This is a dermoscopic photograph of a skin lesion.
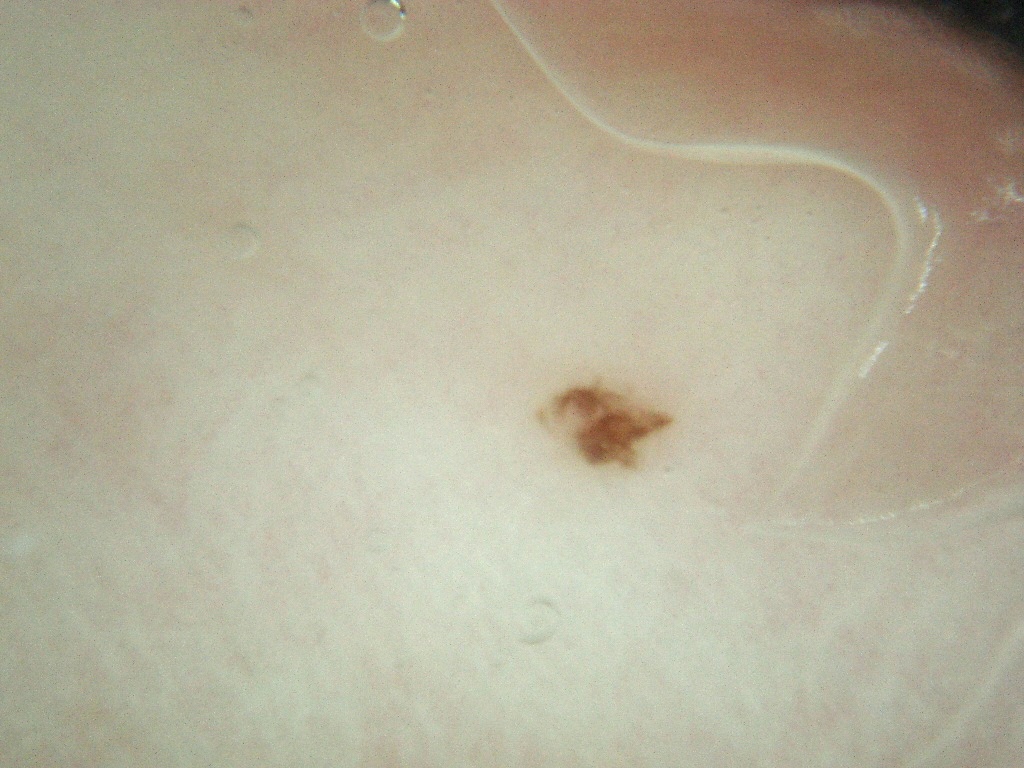Q: Where is the lesion in the image?
A: [535,373,674,470]
Q: Which dermoscopic features are absent?
A: globules and streaks
Q: How much of the field does the lesion occupy?
A: ~1% of the field
Q: What is this lesion?
A: a benign lesion